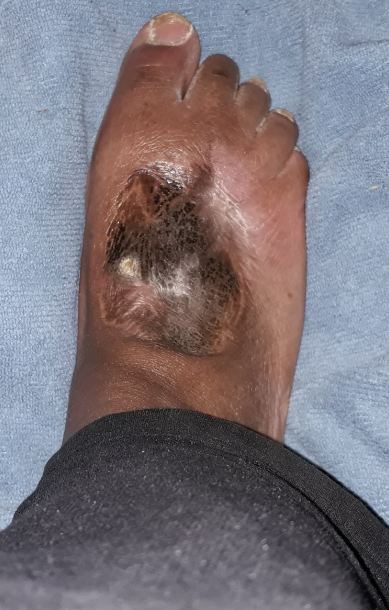Patient information:
The subject is 40–49, male. Located on the top or side of the foot. The photograph was taken at a distance.
Review:
Favoring Foot ulcer.